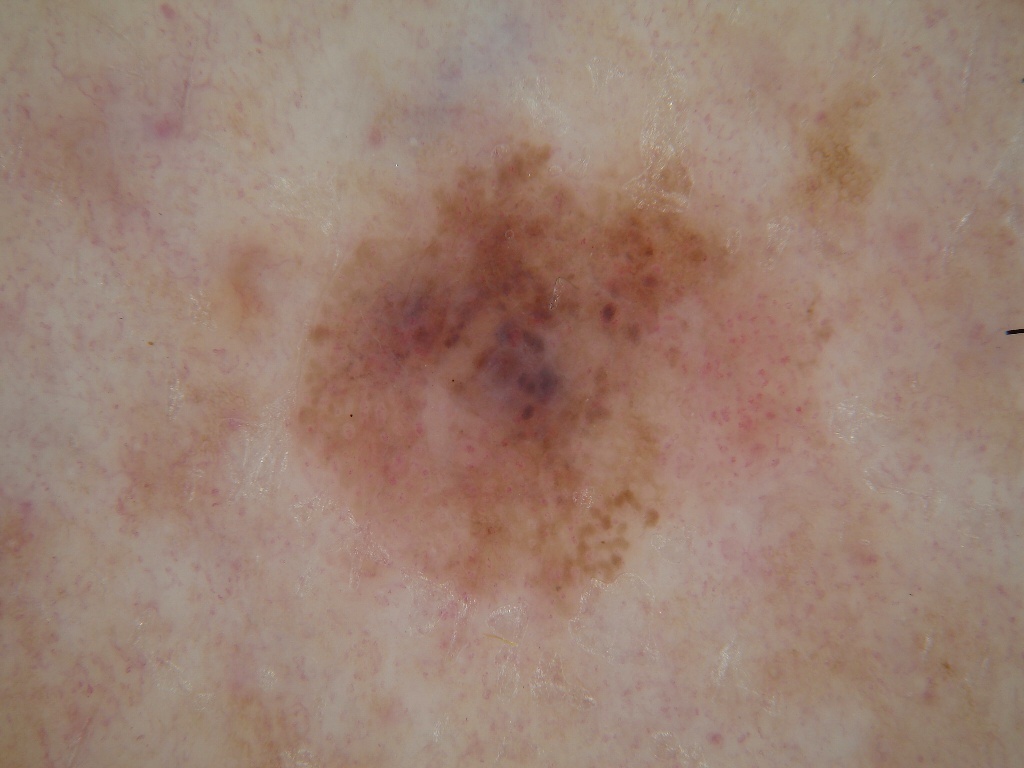image type=dermoscopic image; subject=male, aged 83 or older; bounding box=290/134/831/611; features=globules; lesion size=~20% of the field; assessment=a melanoma, a skin cancer.